Close-up view: 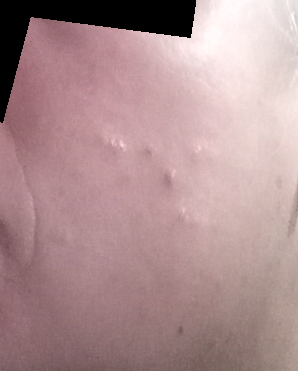Impression:
The skin findings could not be characterized from the image.